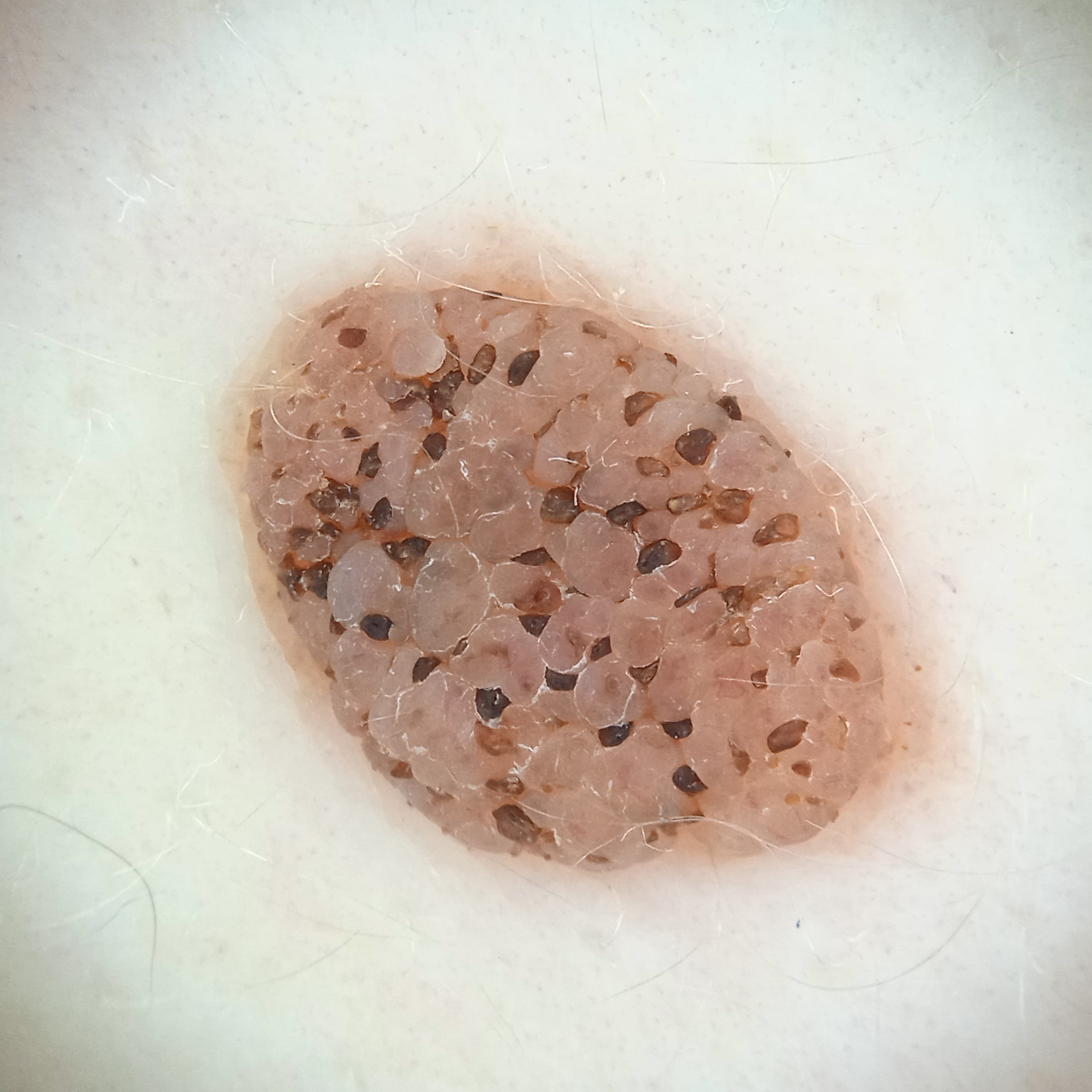Dermoscopy of a skin lesion. The lesion is on the back. The lesion is about 8.4 mm across. The lesion was assessed as a seborrheic keratosis.